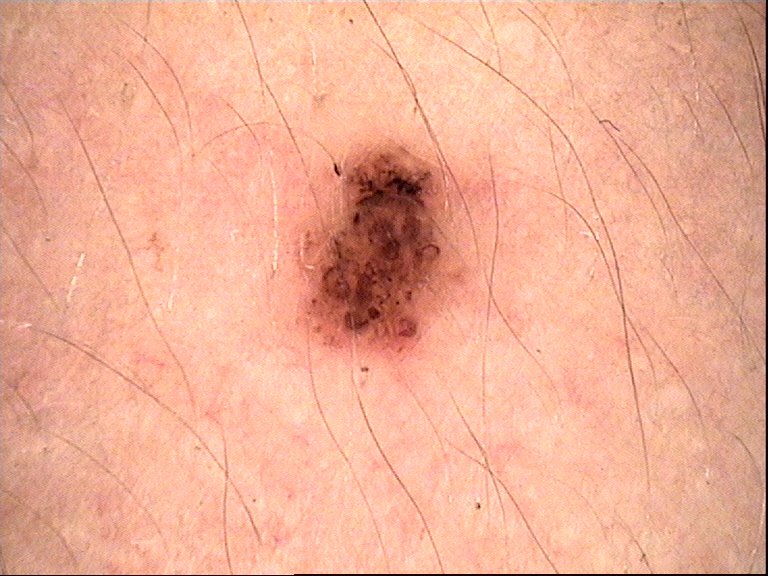Consistent with a dysplastic compound nevus.